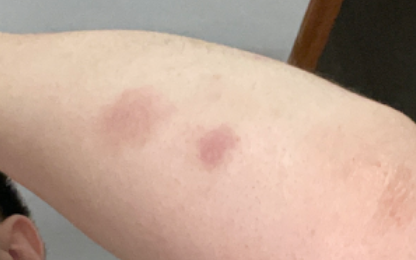  symptoms: darkening
  patient_category: a rash
  body_site: arm
  patient: male, age 18–29
  systemic_symptoms: none reported
  shot_type: at an angle
  differential:
    leading:
      - Eczema
    unlikely:
      - Psoriasis
      - Acute and chronic dermatitis
      - Post-Inflammatory hyperpigmentation